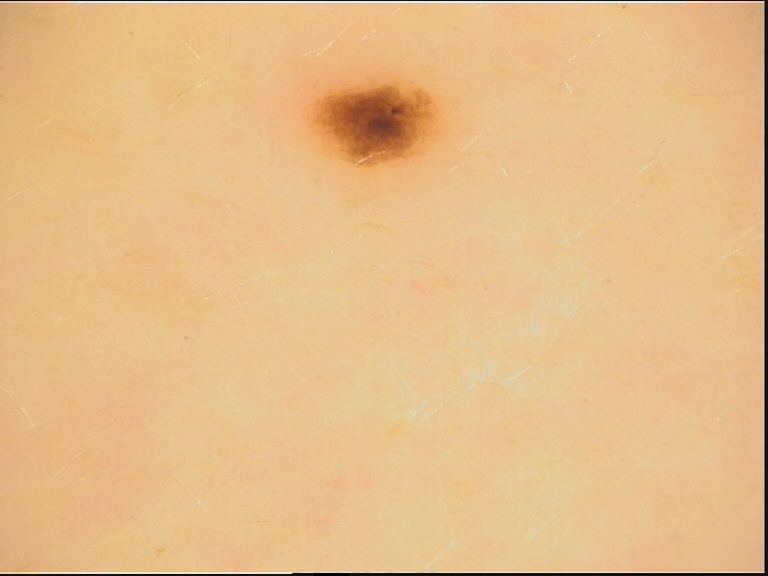A dermoscopic photograph of a skin lesion.
The diagnosis was a benign lesion — a dysplastic junctional nevus.